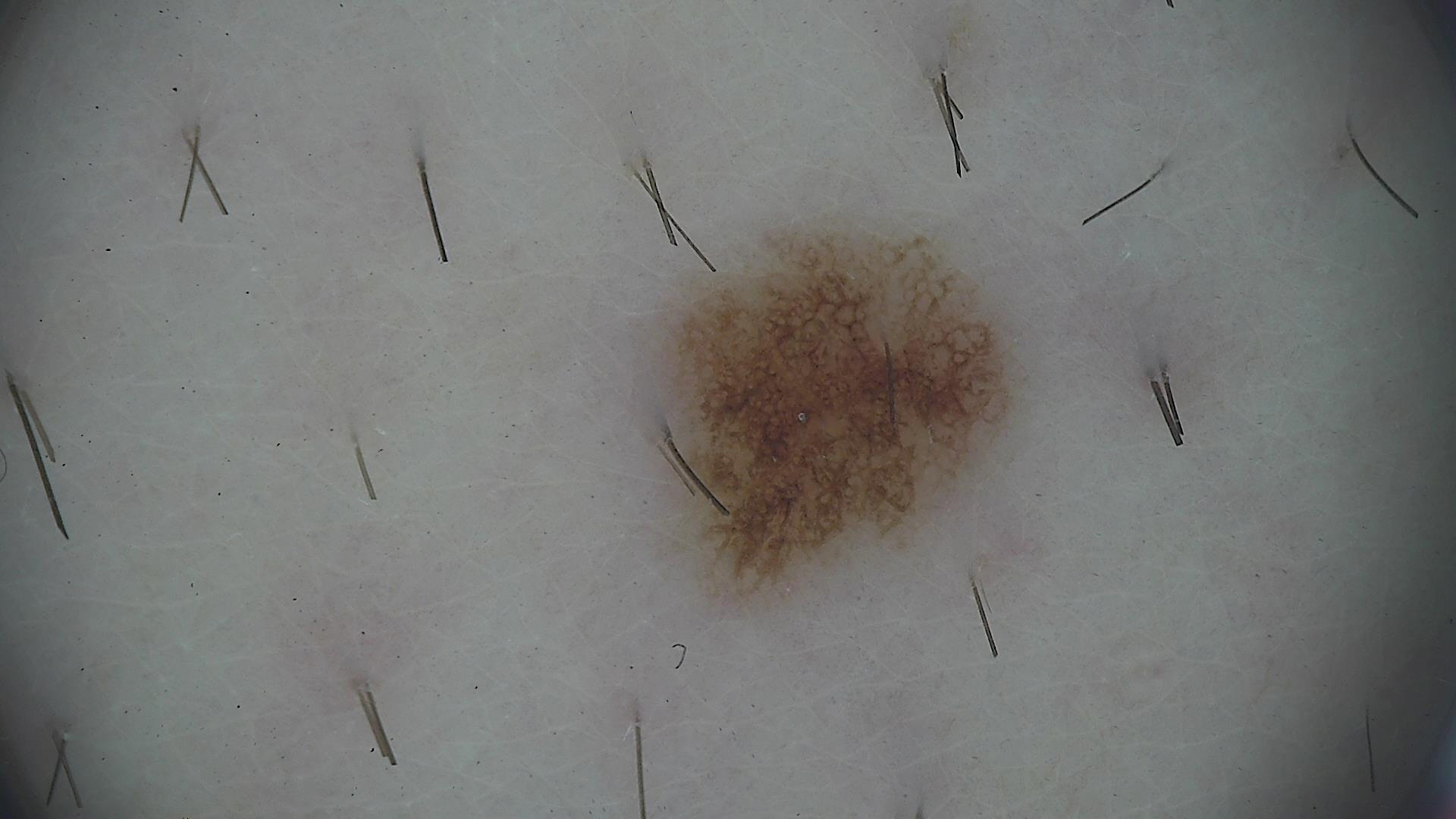A dermoscopic photograph of a skin lesion.
Consistent with a dysplastic junctional nevus.